A skin lesion imaged with a dermatoscope.
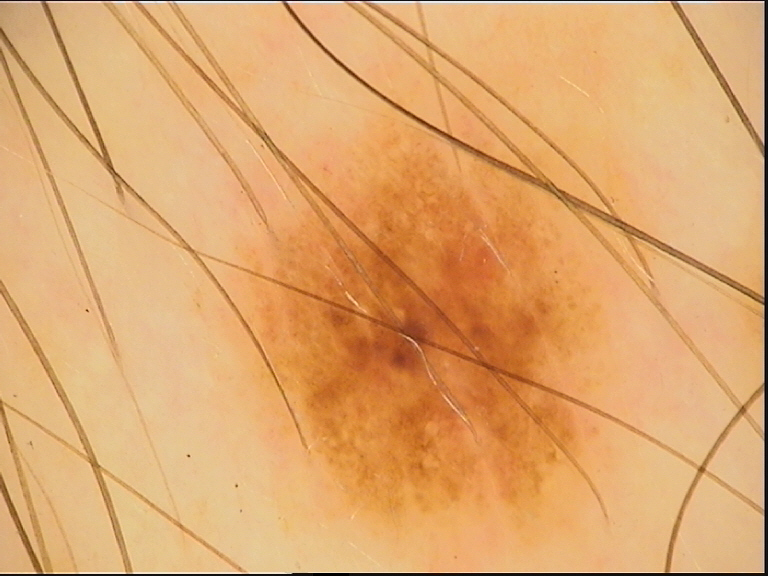Diagnosed as a benign lesion — a dysplastic junctional nevus.